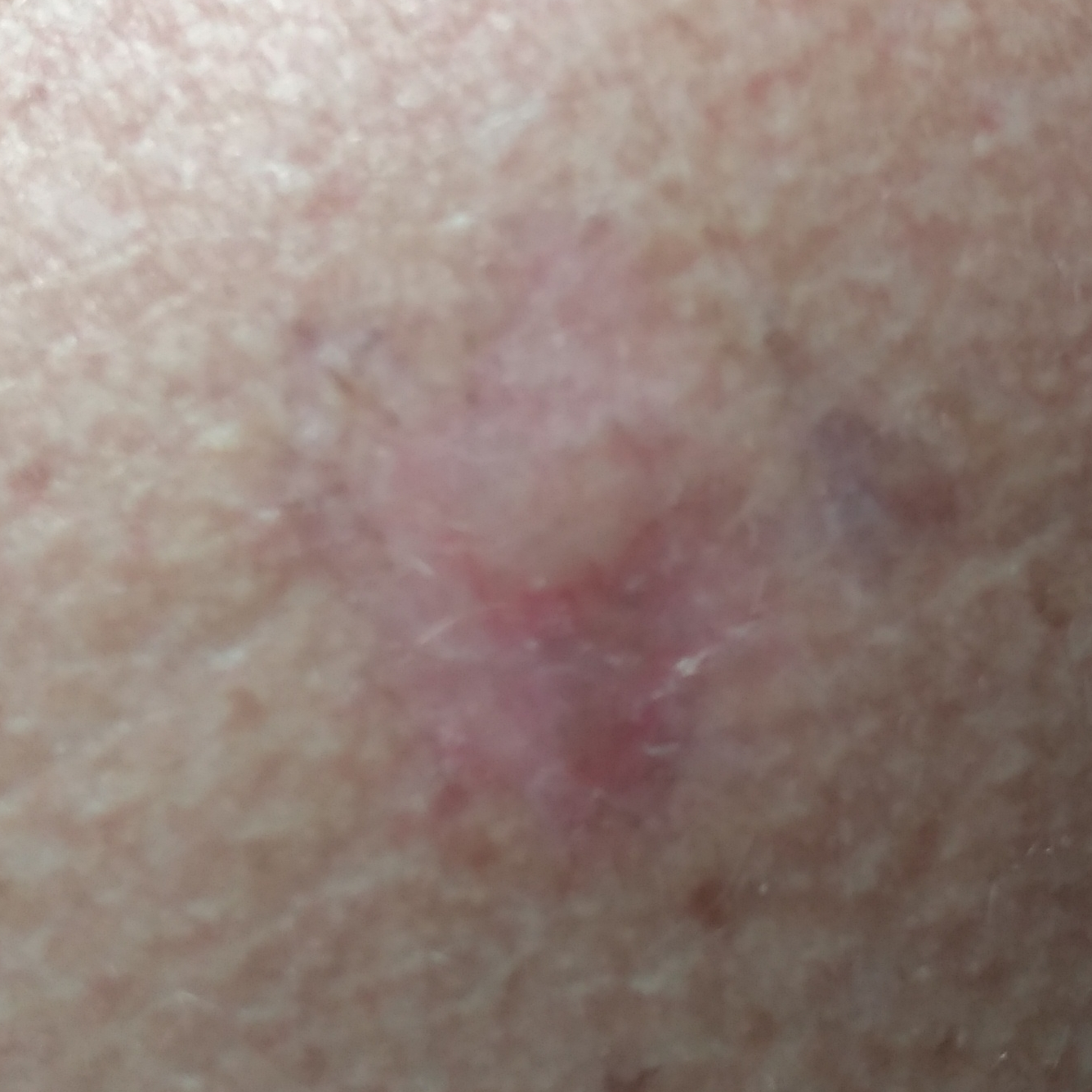risk factors = pesticide exposure, prior skin cancer (patient or family); Fitzpatrick = III; modality = clinical photograph; patient = female, in their early 50s; region = the chest; diameter = 22 × 22 mm; pathology = basal cell carcinoma (biopsy-proven).